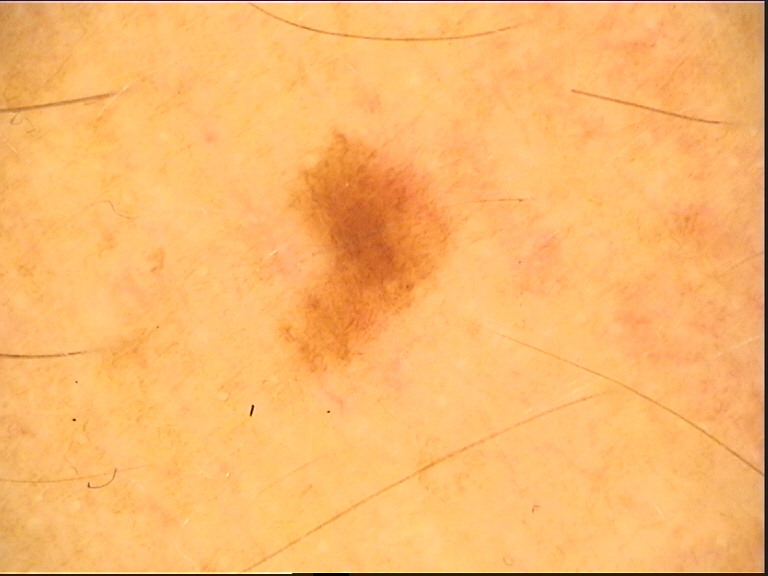Q: What kind of image is this?
A: dermoscopy
Q: What is this lesion?
A: acral dysplastic junctional nevus (expert consensus)